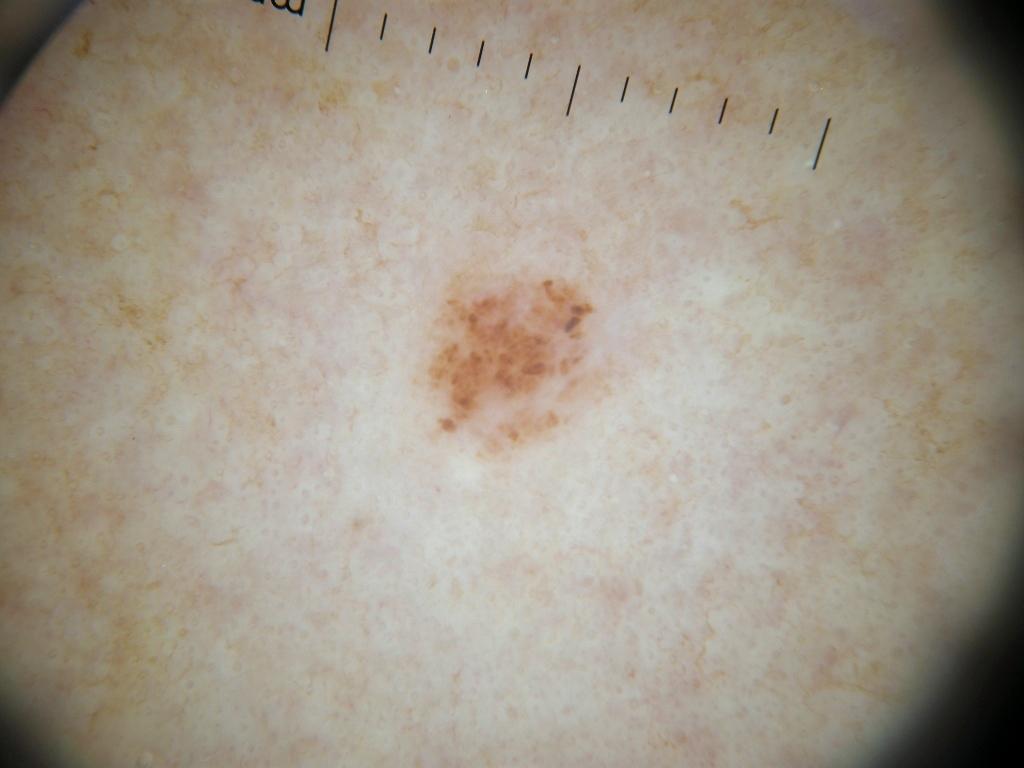patient = female, roughly 75 years of age | modality = dermoscopic image | absent dermoscopic findings = negative network, globules, pigment network, streaks, and milia-like cysts | lesion size = small | location = left=394, top=246, right=648, bottom=492 | assessment = a melanocytic nevus.